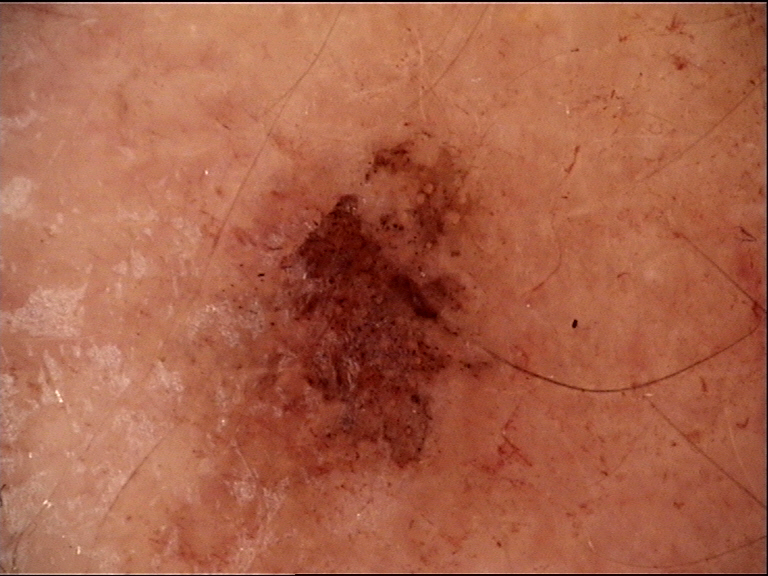A skin lesion imaged with a dermatoscope. The diagnosis was a benign lesion — a dysplastic compound nevus.